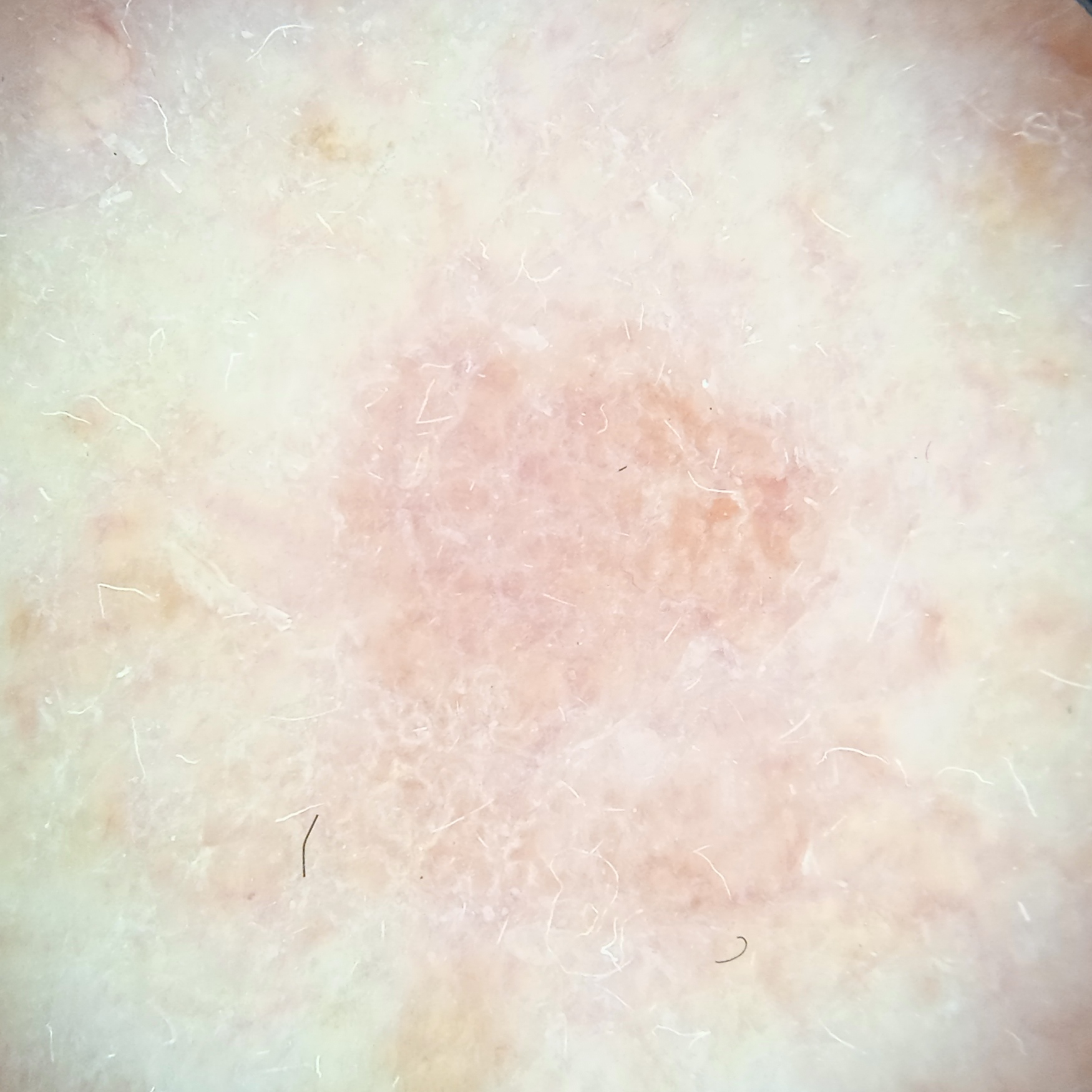modality — dermatoscopic image; clinical context — clinical suspicion of basal cell carcinoma; sun reaction — skin reddens painfully with sun exposure; relevant history — immunosuppression, a prior organ transplant, no personal history of skin cancer; subject — female, age 55; location — the face; diameter — 5.7 mm; diagnostic label — actinic keratosis (dermatologist consensus).